A skin lesion imaged with a dermatoscope.
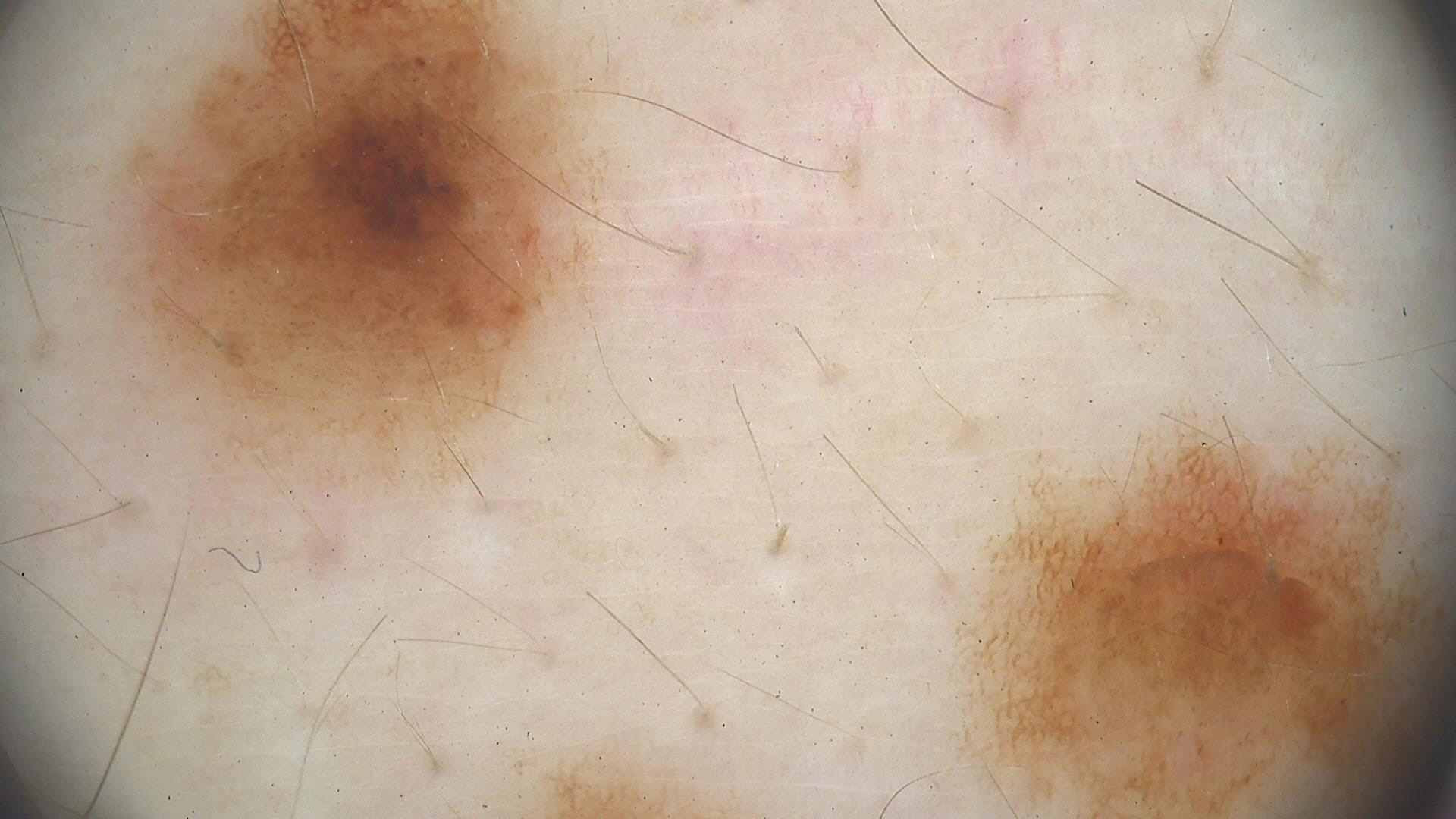Diagnosed as a dysplastic junctional nevus.